A dermatoscopic image of a skin lesion.
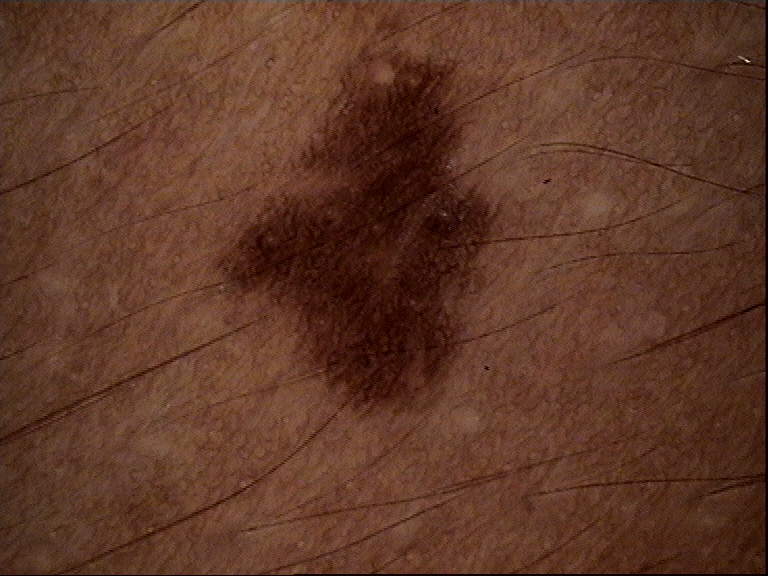Q: What was the diagnostic impression?
A: dysplastic junctional nevus (expert consensus)